The affected area is the leg · this image was taken at an angle.
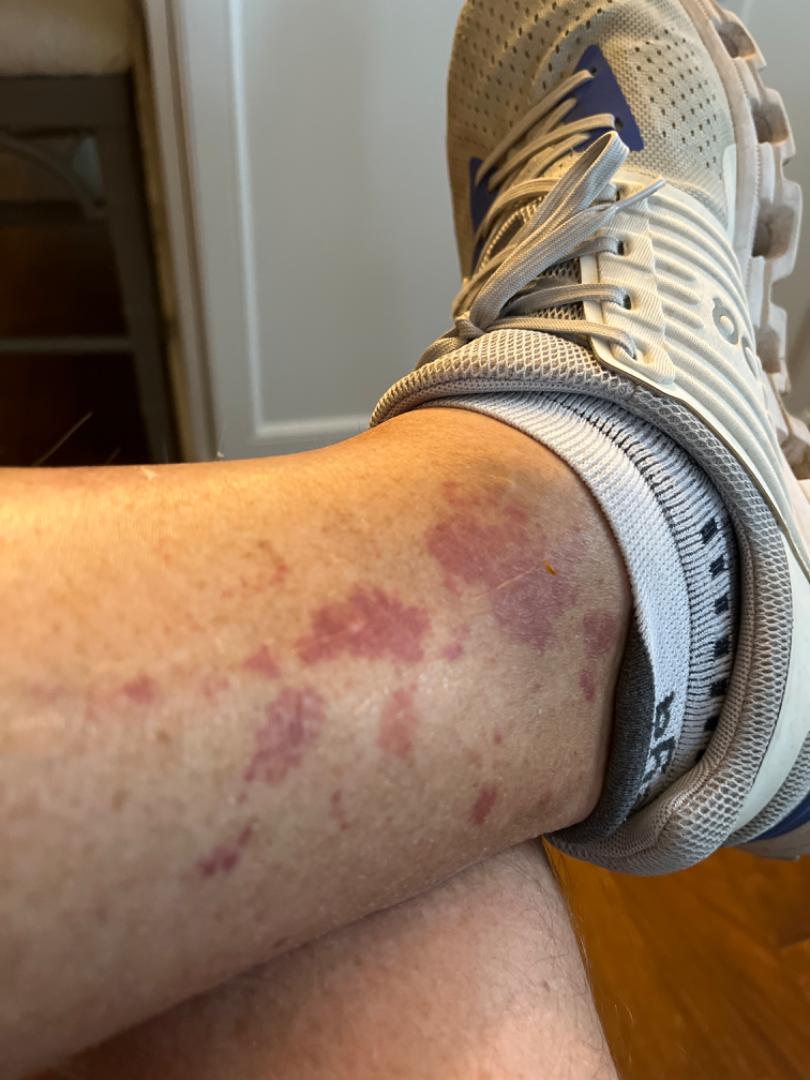{"assessment": "not assessable"}